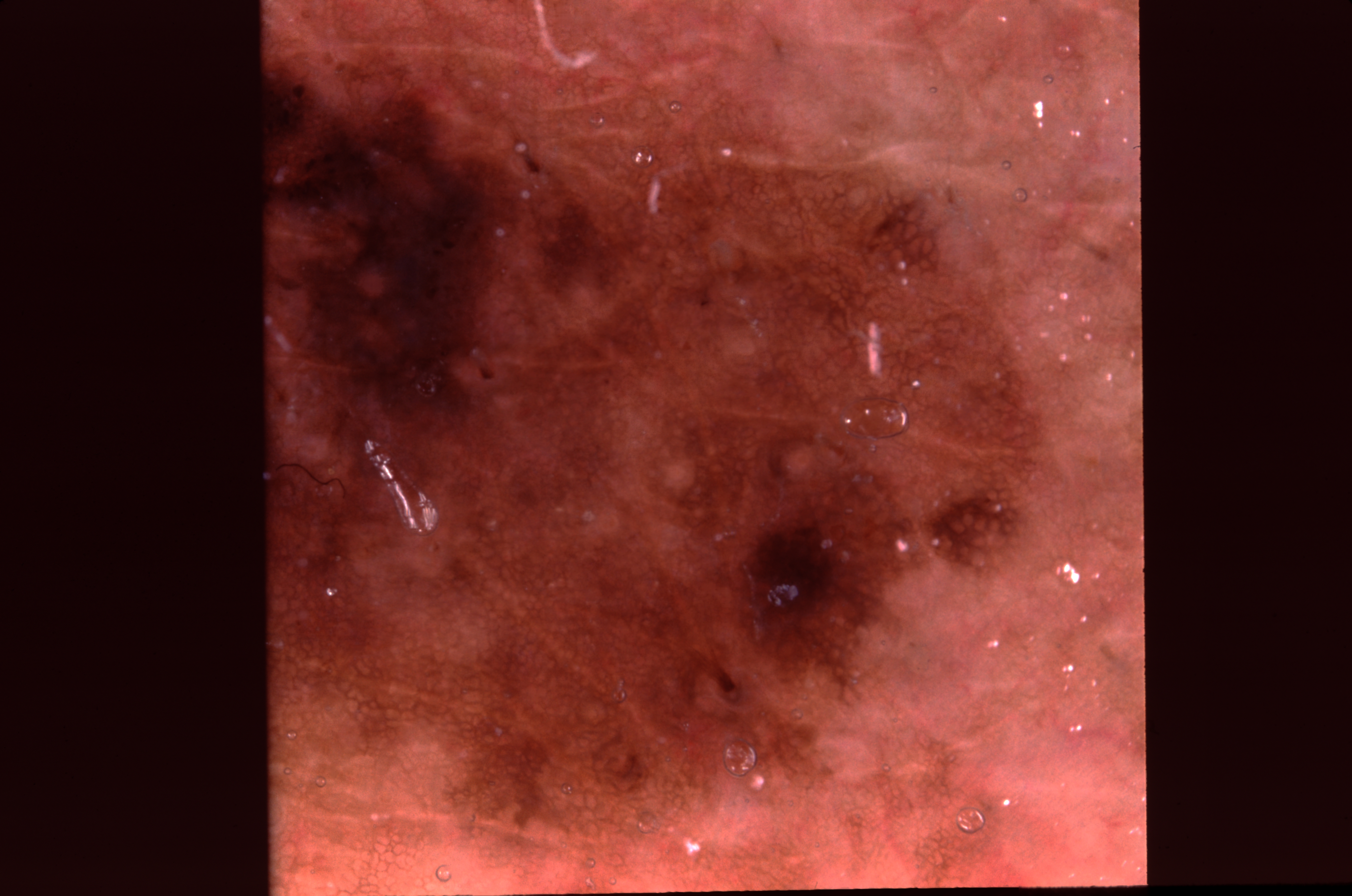Q: What are the patient's age and sex?
A: male
Q: How was this image acquired?
A: dermoscopy
Q: Where is the lesion located?
A: 261 2 1077 872
Q: What dermoscopic features are present?
A: pigment network
Q: What is this lesion?
A: a melanocytic nevus